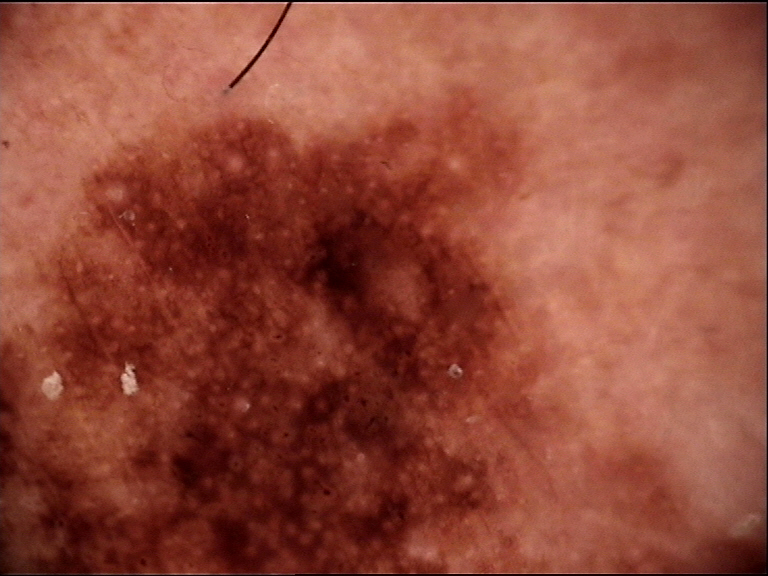{"image": "dermatoscopy", "diagnosis": {"name": "lentigo maligna", "code": "lm", "malignancy": "malignant", "super_class": "melanocytic", "confirmation": "histopathology"}}